The contributor is female; the patient described the issue as a rash; the leg is involved; the patient reports the lesion is fluid-filled and raised or bumpy; the photograph is a close-up of the affected area; no associated systemic symptoms reported.
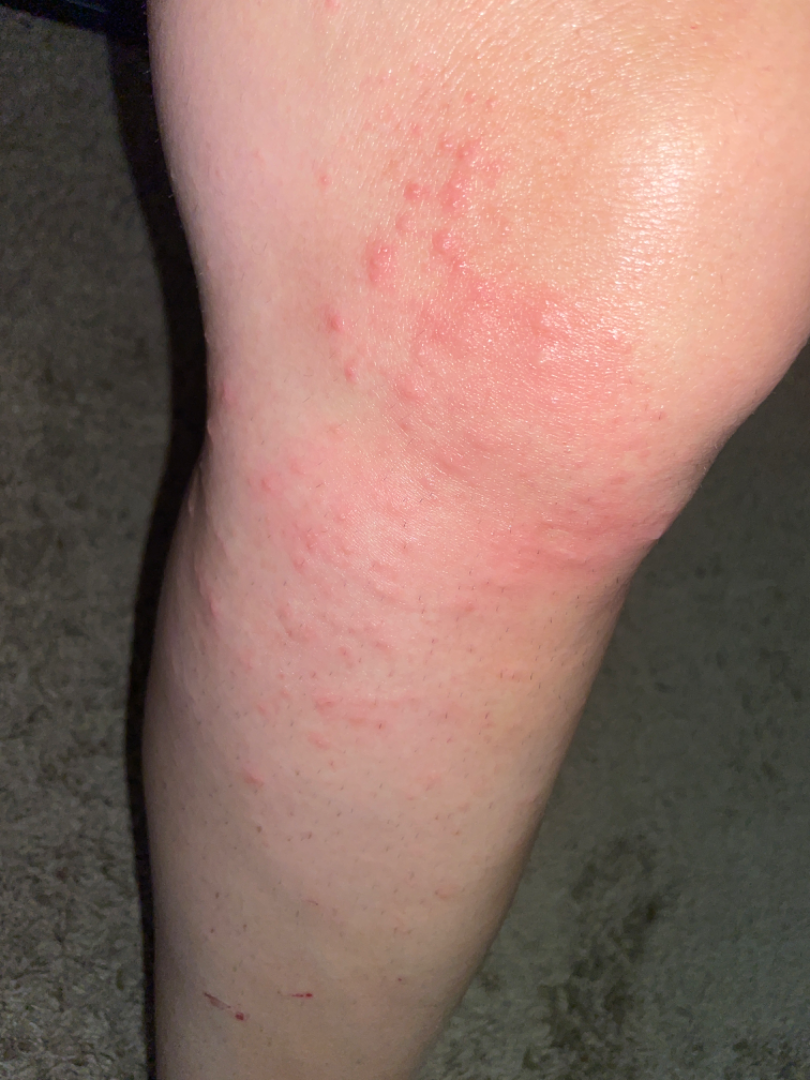Findings: On photographic review, most likely Eczema; also consider Insect Bite; possibly Allergic Contact Dermatitis.